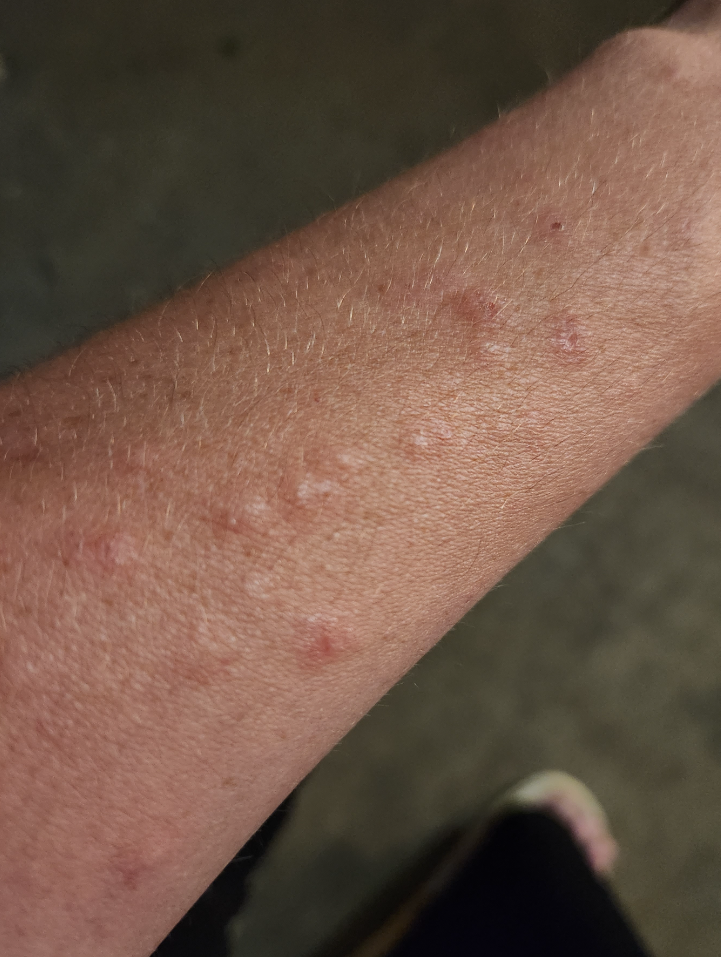Q: What was the assessment?
A: could not be assessed
Q: How long has this been present?
A: one to four weeks
Q: What symptoms does the patient report?
A: burning, itching, enlargement and pain
Q: Patient's own categorization?
A: a rash
Q: Texture?
A: fluid-filled and raised or bumpy
Q: How was the photo taken?
A: close-up
Q: What is the affected area?
A: head or neck and leg